Self-categorized by the patient as a rash; close-up view; self-reported Fitzpatrick IV; male subject, age 18–29; the lesion involves the top or side of the foot; symptoms reported: itching; present for less than one week; the lesion is described as raised or bumpy.
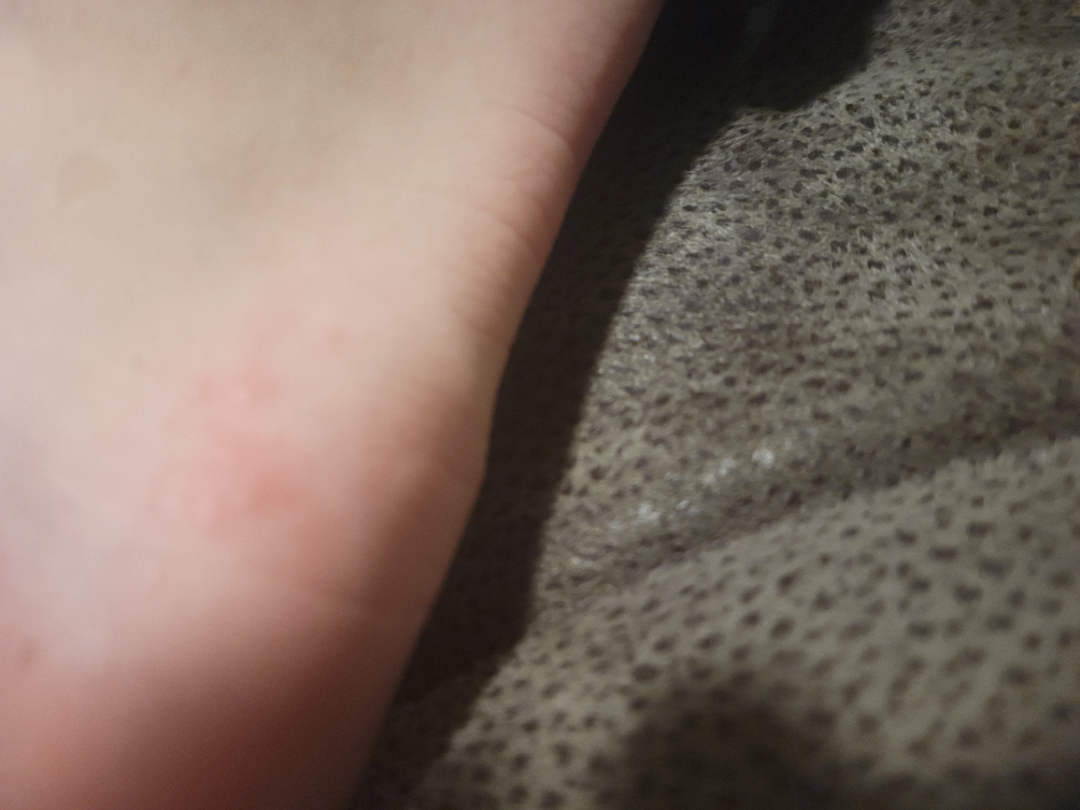assessment = not assessable